A male subject, aged approximately 30. A dermoscopic image of a skin lesion:
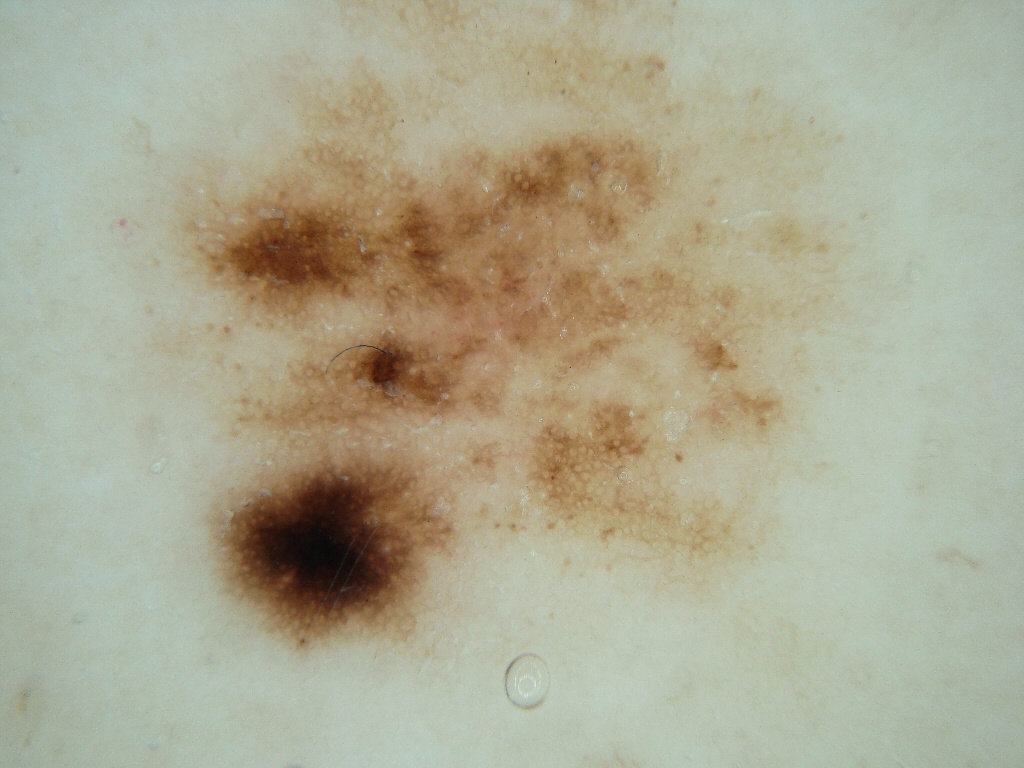The lesion is bounded by box(83, 2, 924, 664). The dermoscopic pattern shows pigment network and globules. Expert review diagnosed this as a melanocytic nevus, a benign skin lesion.